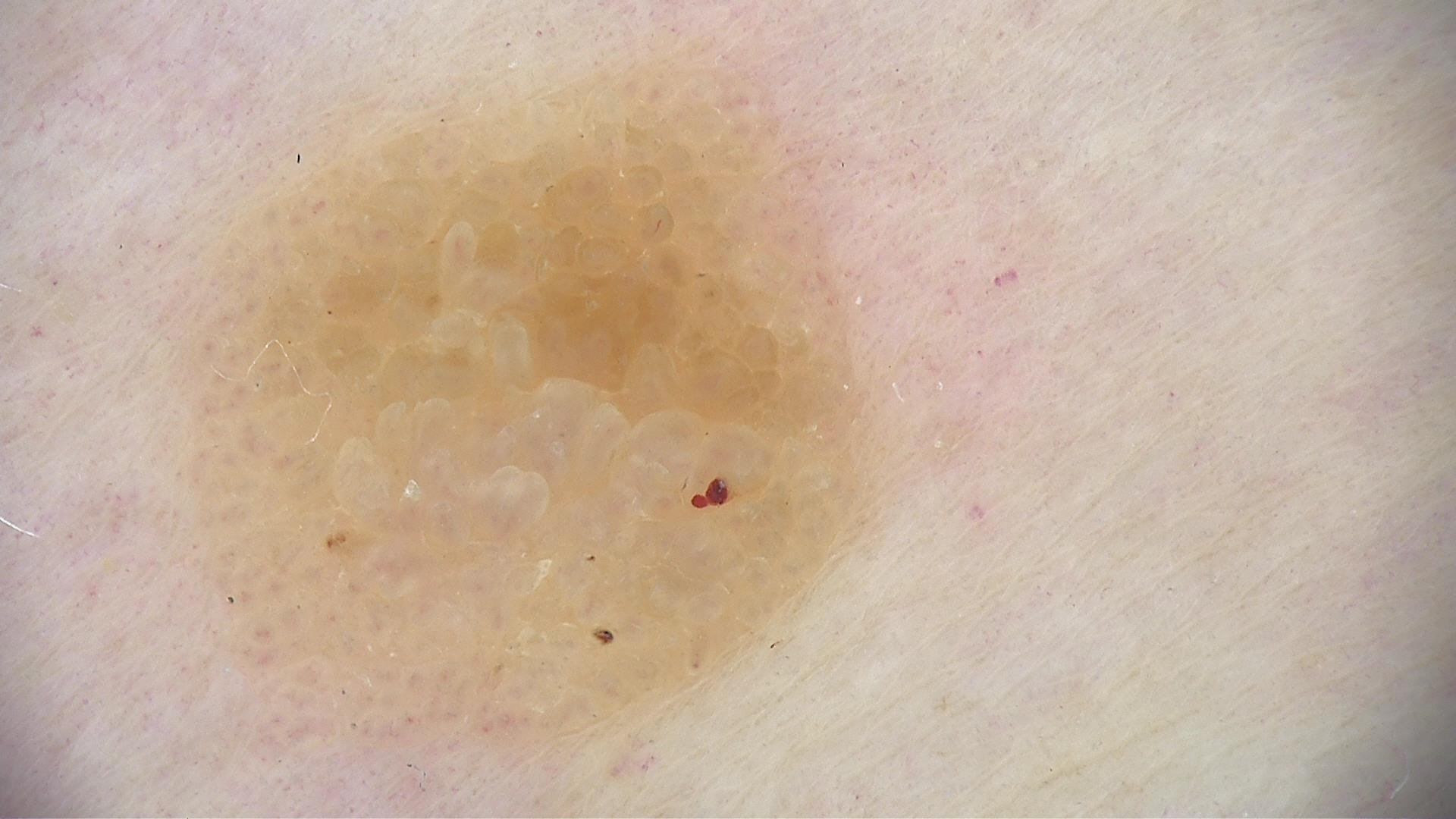A skin lesion imaged with a dermatoscope.
Classified as a keratinocytic, benign lesion — a seborrheic keratosis.